Acquired for a research image collection, with no referral diagnosis; a male subject 54 years of age; the patient reports a personal history of cancer; the patient says their skin tans without first burning; a clinical photograph showing a skin lesion; a moderate number of moles by the patient's own estimate.
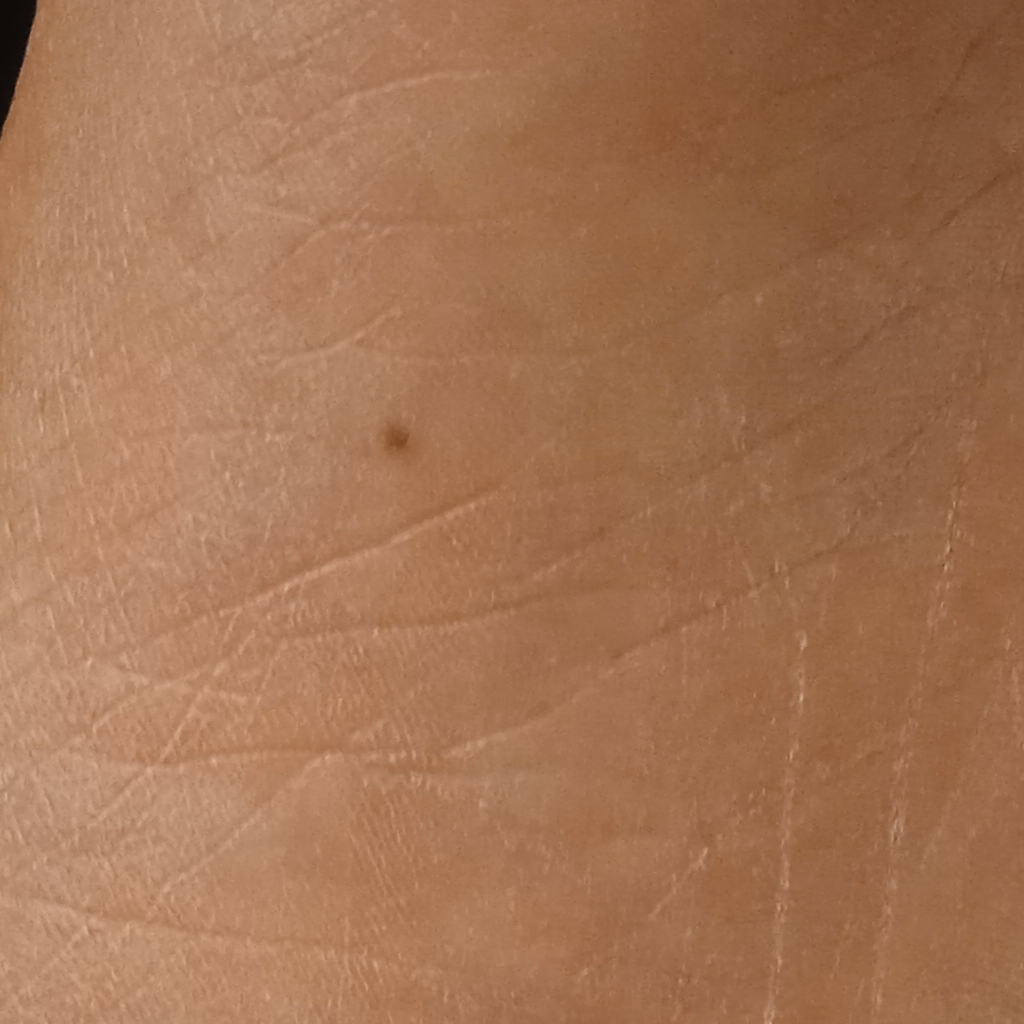| feature | finding |
|---|---|
| anatomic site | a leg |
| size | 2.2 mm |
| diagnosis | melanocytic nevus (dermatologist consensus) |